A subject age 12 · a clinical photo of a skin lesion taken with a smartphone:
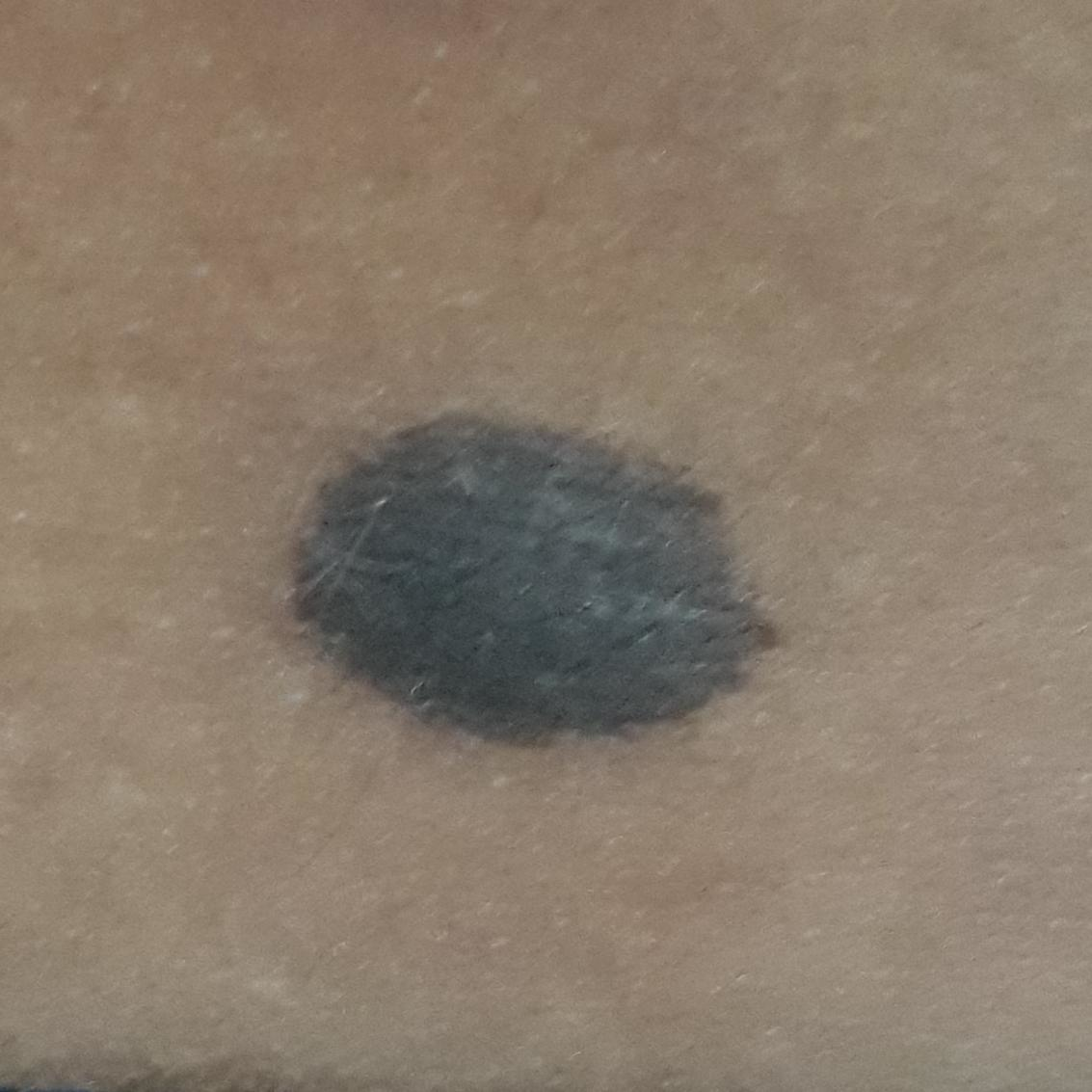The lesion was found on the back.
The patient reports that the lesion is elevated and has grown.
The diagnostic impression was a nevus.